The photograph was taken at an angle.
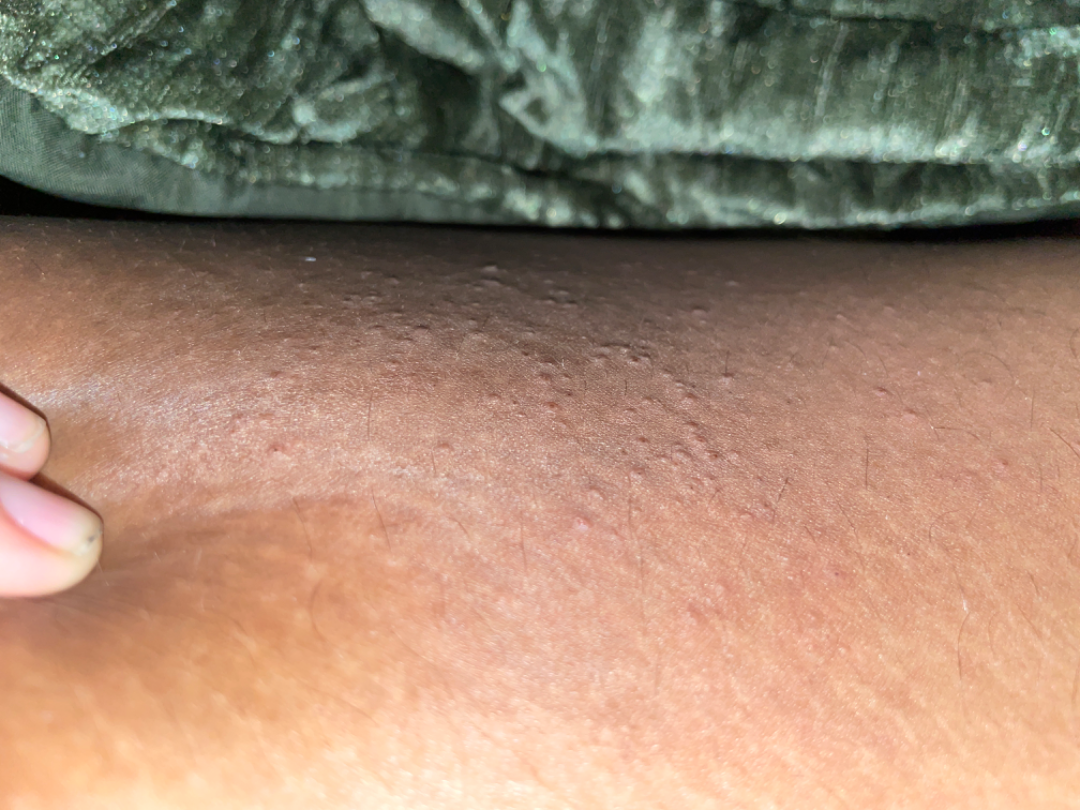The case was indeterminate on photographic review.